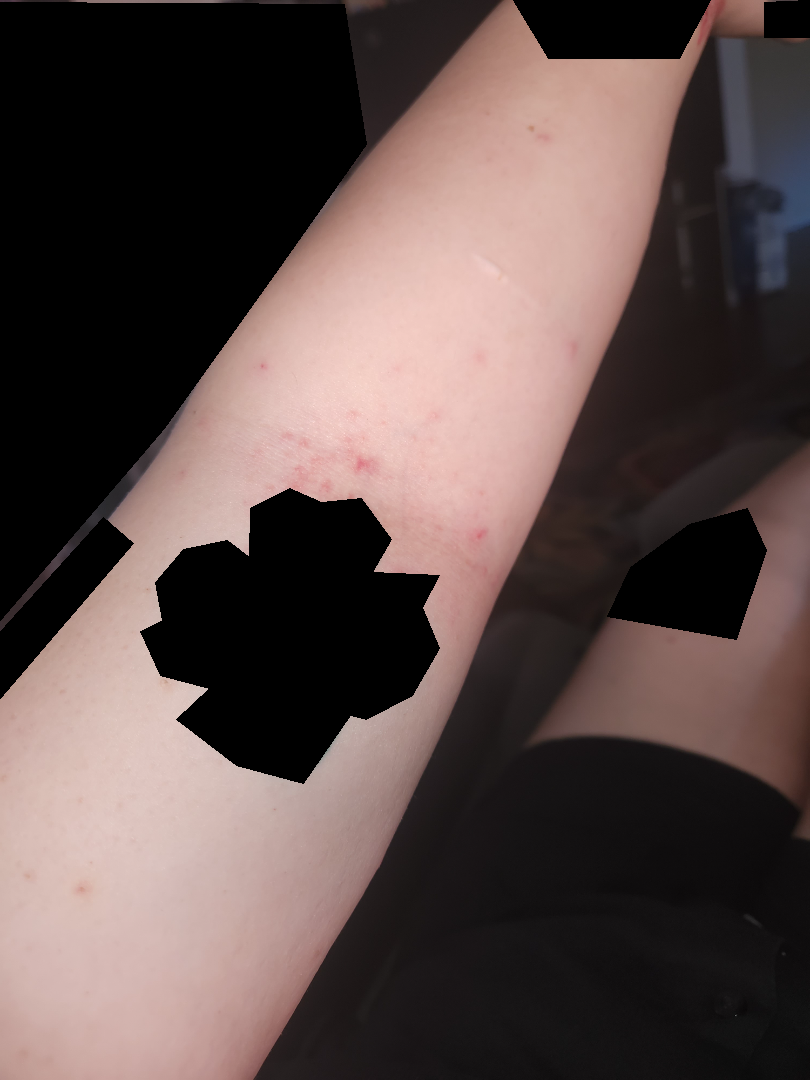body site = arm, framing = at a distance, assessment = Eczema (weight 1.00).